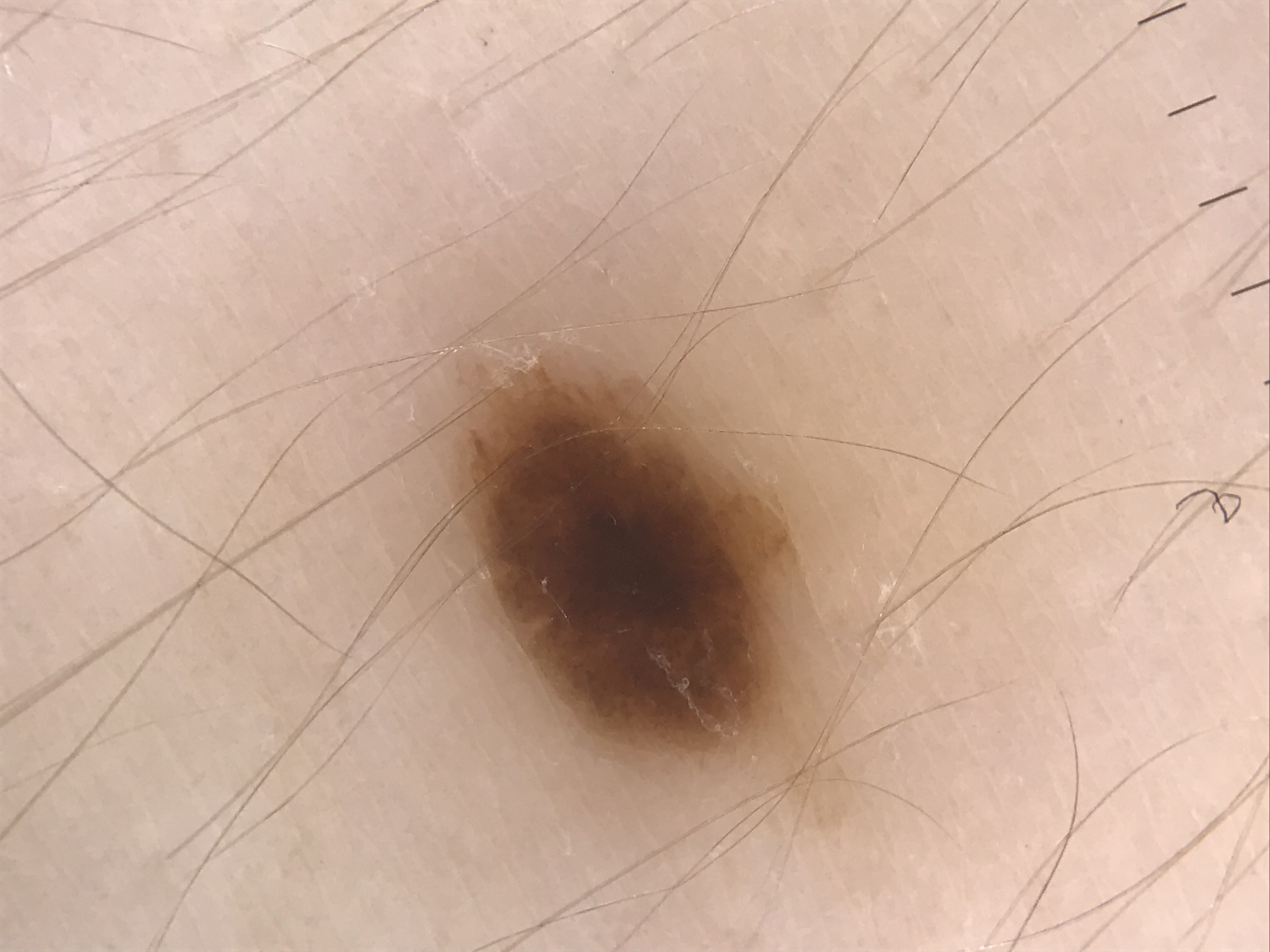Case: A dermoscopic close-up of a skin lesion. Conclusion: Diagnosed as a benign lesion — a dysplastic compound nevus.